On a questionnaire the patient reported a personal history of cancer, a personal history of skin cancer, no family history of skin cancer, and no prior organ transplant · a dermoscopic image of a skin lesion · a female patient aged 60 · the patient says their skin tans without first burning · few moles overall by the patient's own estimate · referred for assessment of suspected basal cell carcinoma.
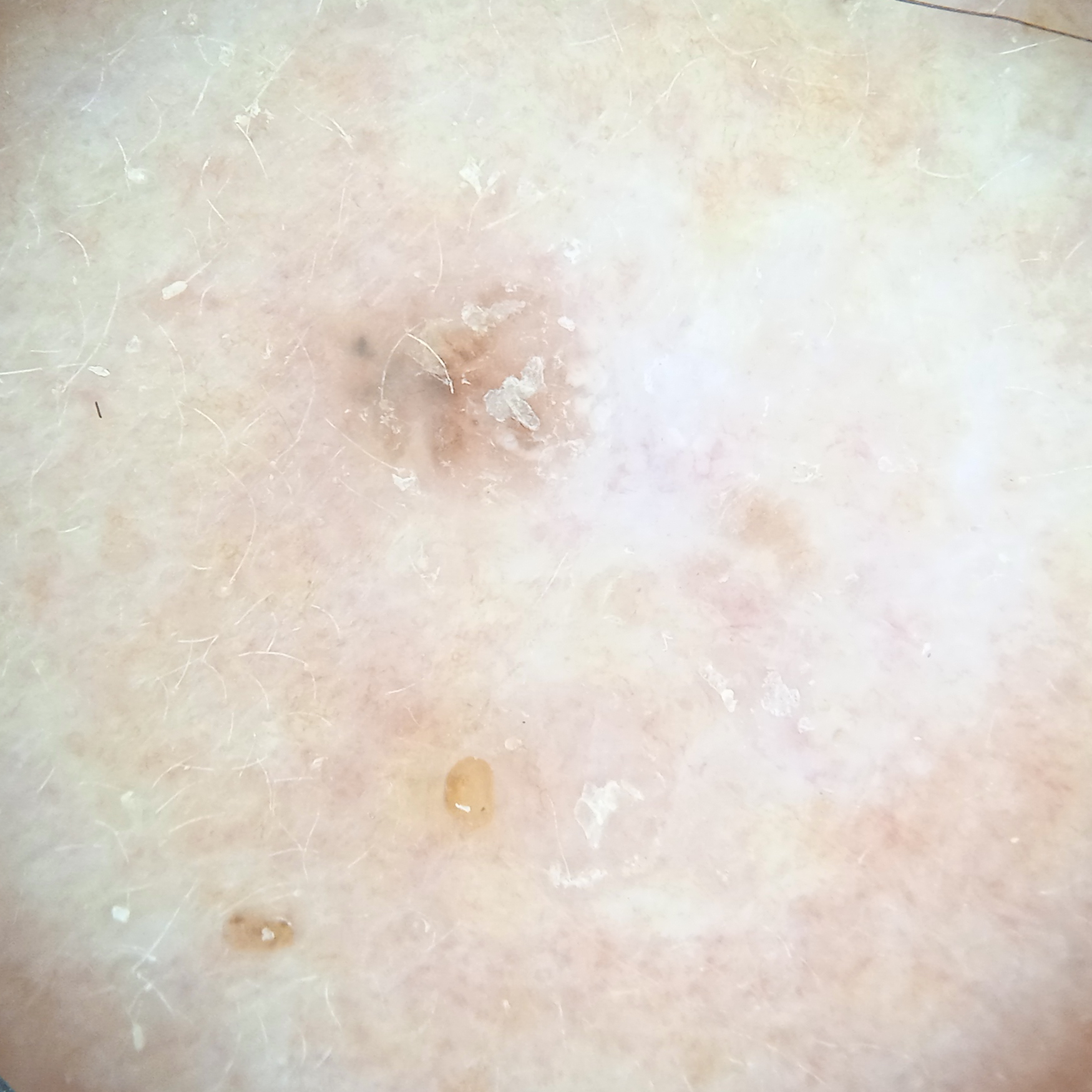The lesion involves the face. Histopathologically confirmed as a basal cell carcinoma, following excision, with a measured tumor thickness of 1 mm.